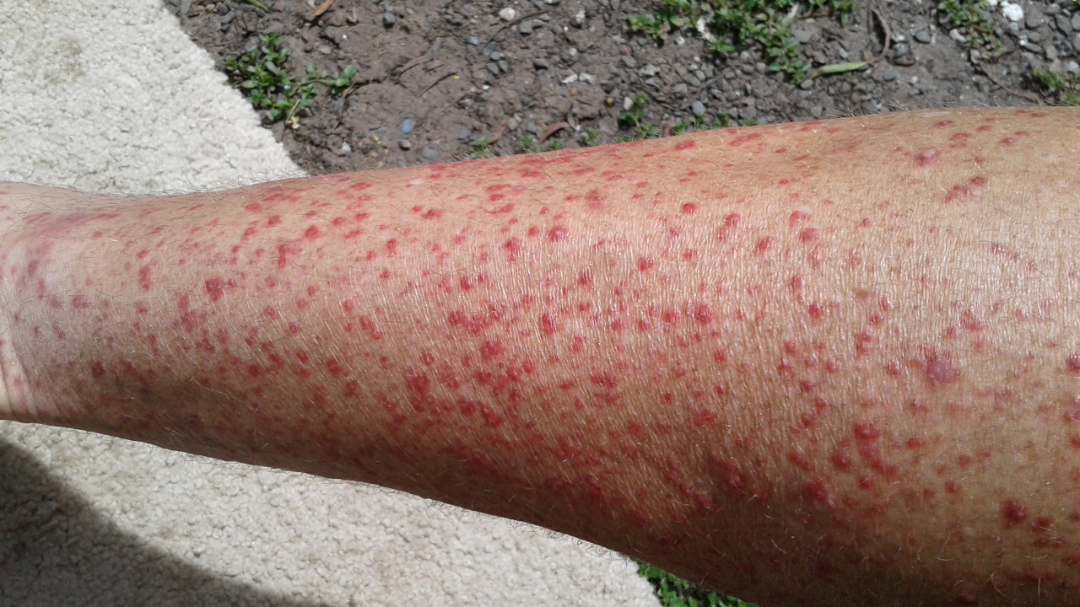patient = male, age 50–59
patient-reported symptoms = bothersome appearance, enlargement and itching
constitutional symptoms = fatigue
framing = close-up
duration = one to four weeks
lesion texture = raised or bumpy
site = back of the hand, arm, head or neck, palm and leg
patient describes the issue as = skin that appeared healthy to them
differential = three dermatologists independently reviewed the case: the leading consideration is Leukocytoclastic Vasculitis; less likely is Psoriasis; less probable is Eczema